Self-categorized by the patient as a rash. The patient notes the lesion is raised or bumpy. Reported duration is about one day. The patient notes itching. FST IV. Female contributor, age 18–29. This image was taken at an angle — 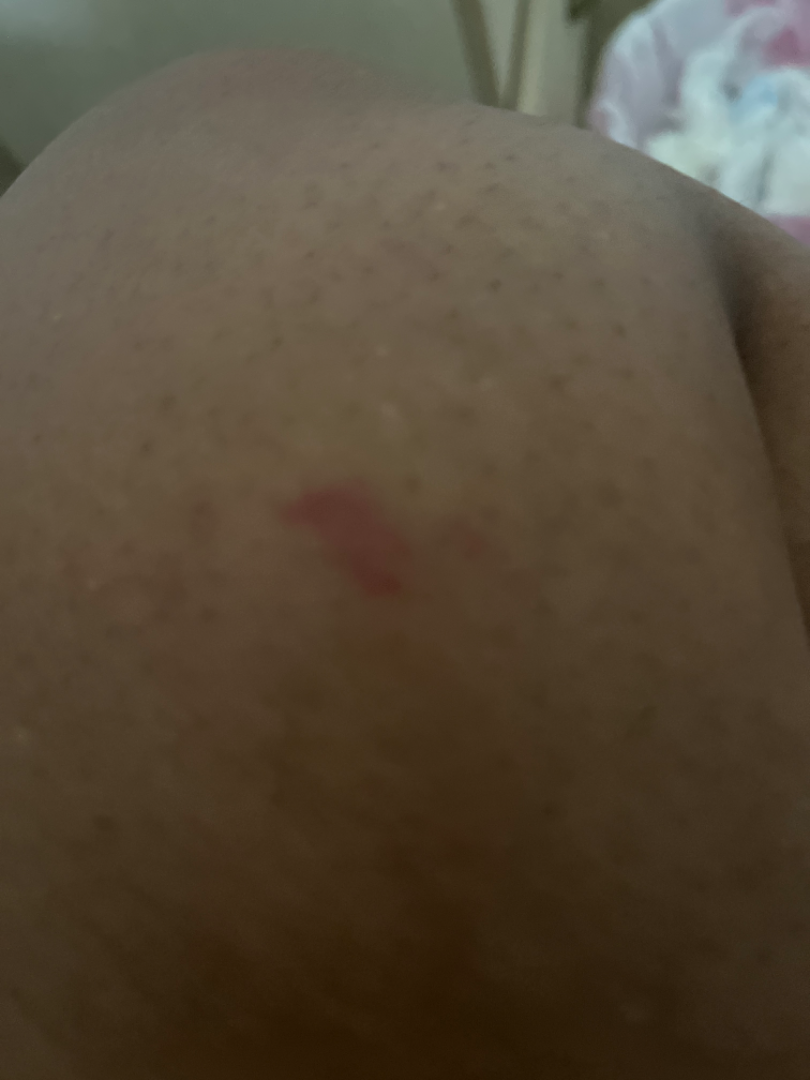The reviewer was unable to grade this case for skin condition.